A dermoscopy image of a single skin lesion · a female subject about 50 years old: 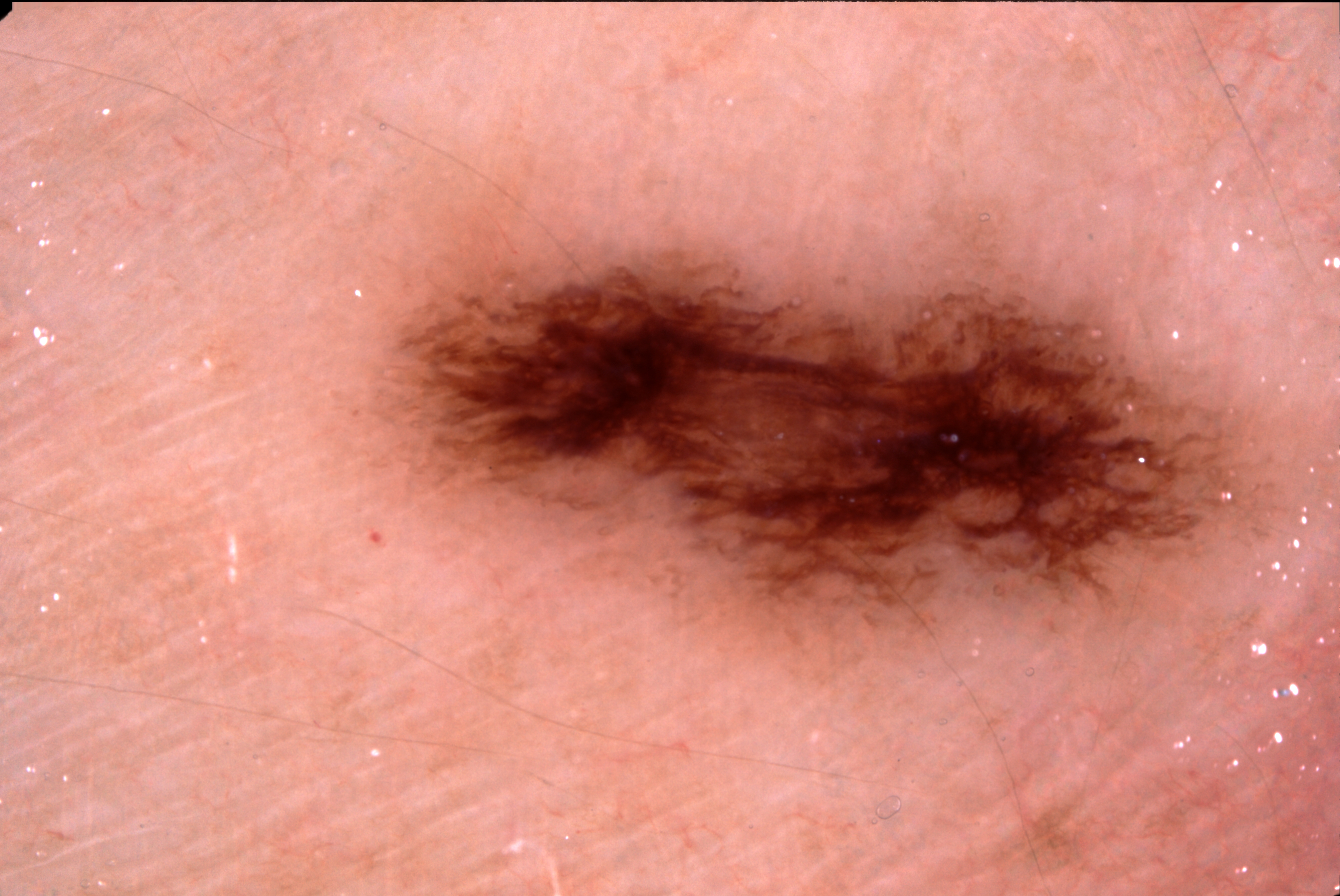As (left, top, right, bottom), the lesion spans <bbox>398, 238, 1246, 637</bbox>.
Dermoscopic assessment notes pigment network; no milia-like cysts, negative network, or streaks.
Expert review diagnosed this as a melanocytic nevus.